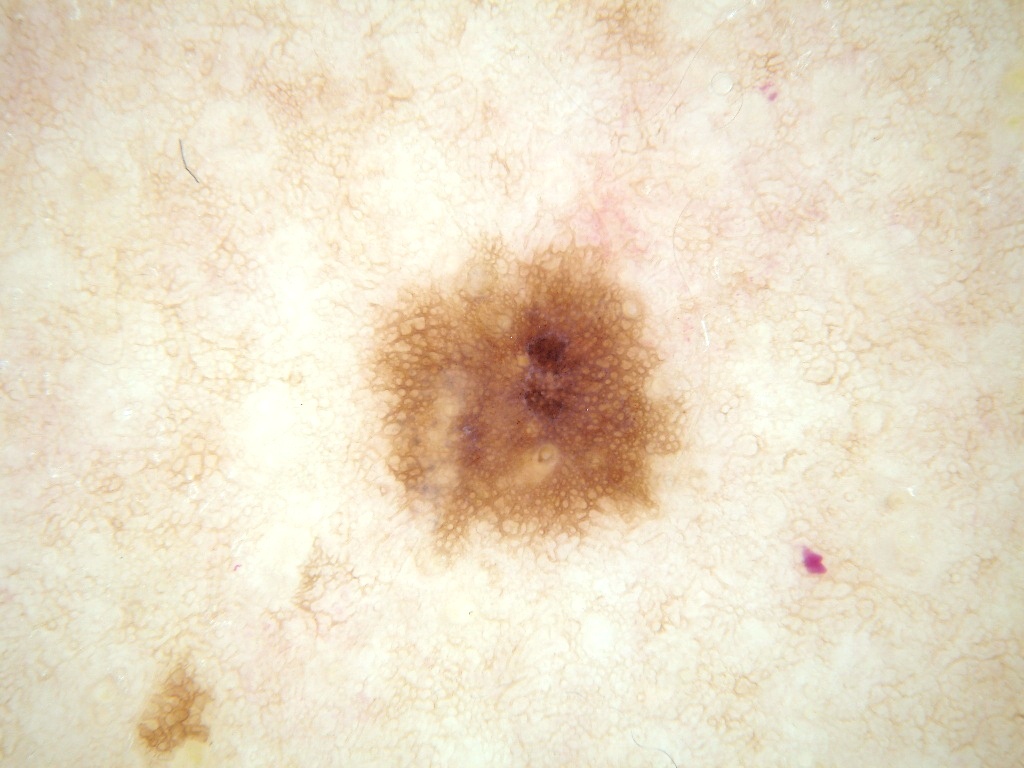This is a dermoscopic photograph of a skin lesion. A female patient, aged 53-57. The dermoscopic pattern shows pigment network, with no globules, milia-like cysts, negative network, or streaks. A mid-sized lesion within the field. As (left, top, right, bottom), lesion location: <box>338, 199, 704, 586</box>. Diagnosed as a melanocytic nevus.